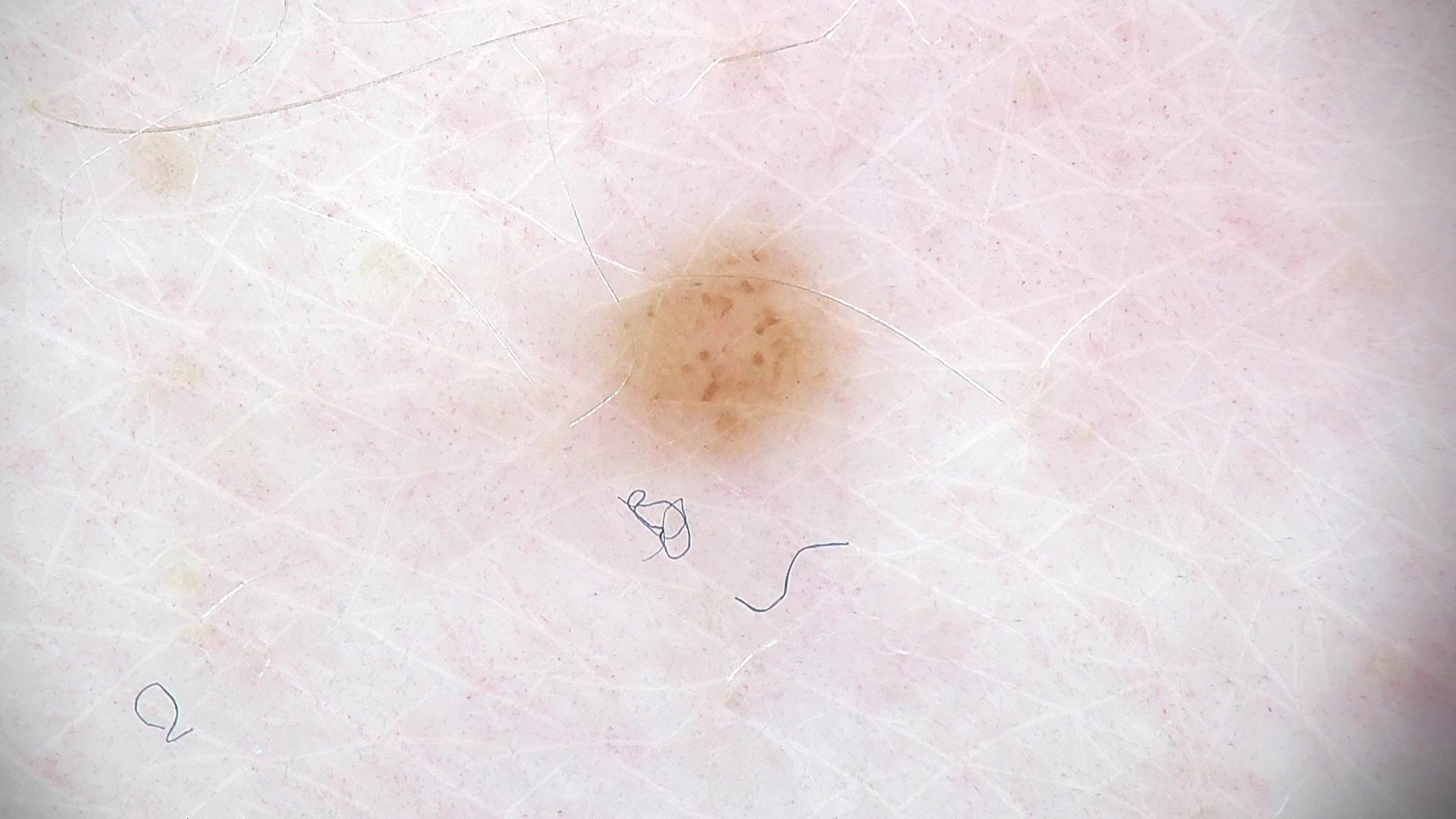{"image": "dermatoscopy", "diagnosis": {"name": "junctional nevus", "code": "jb", "malignancy": "benign", "super_class": "melanocytic", "confirmation": "expert consensus"}}